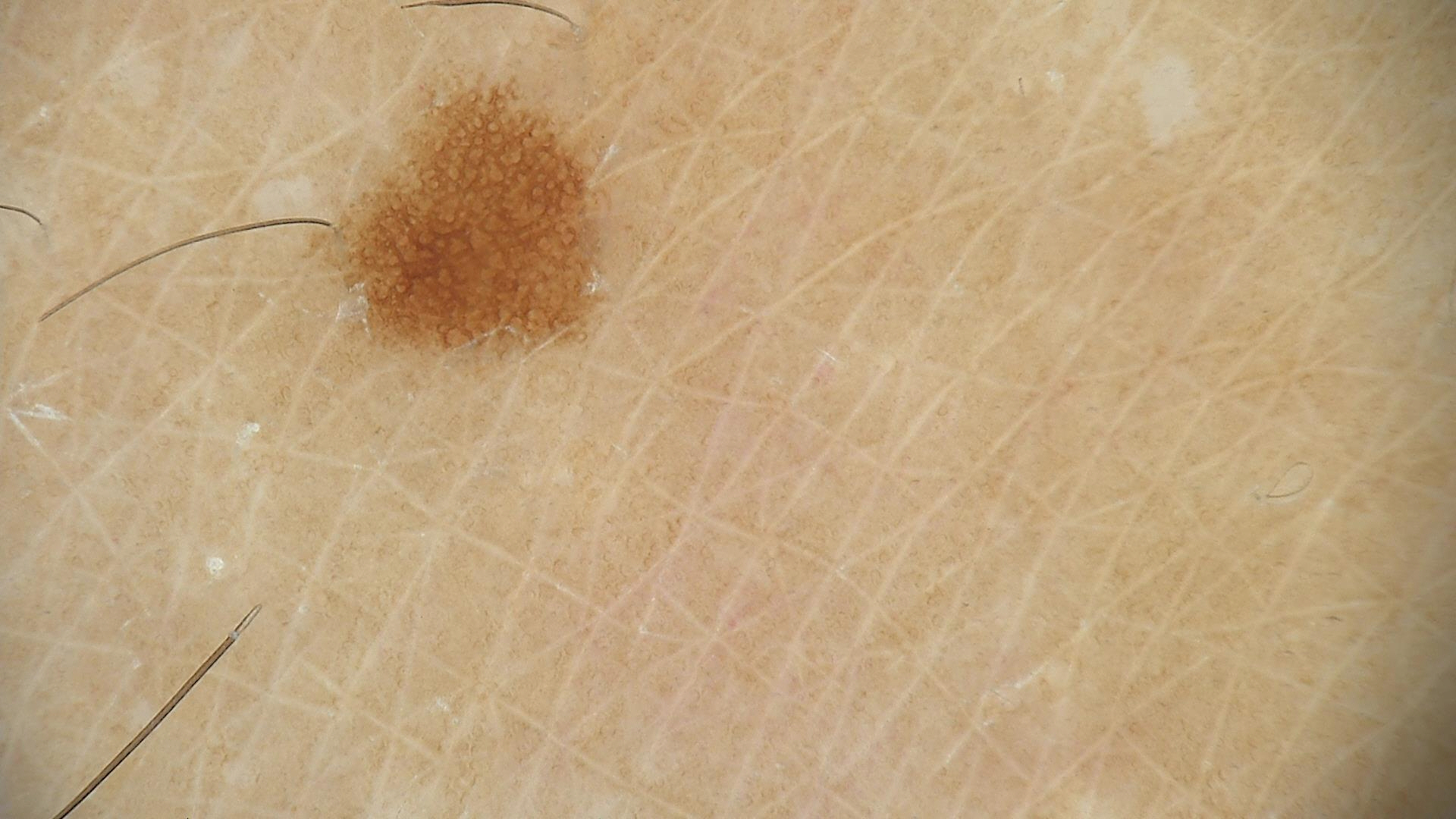Q: What is the diagnosis?
A: dysplastic junctional nevus (expert consensus)